A dermoscopy image of a single skin lesion: 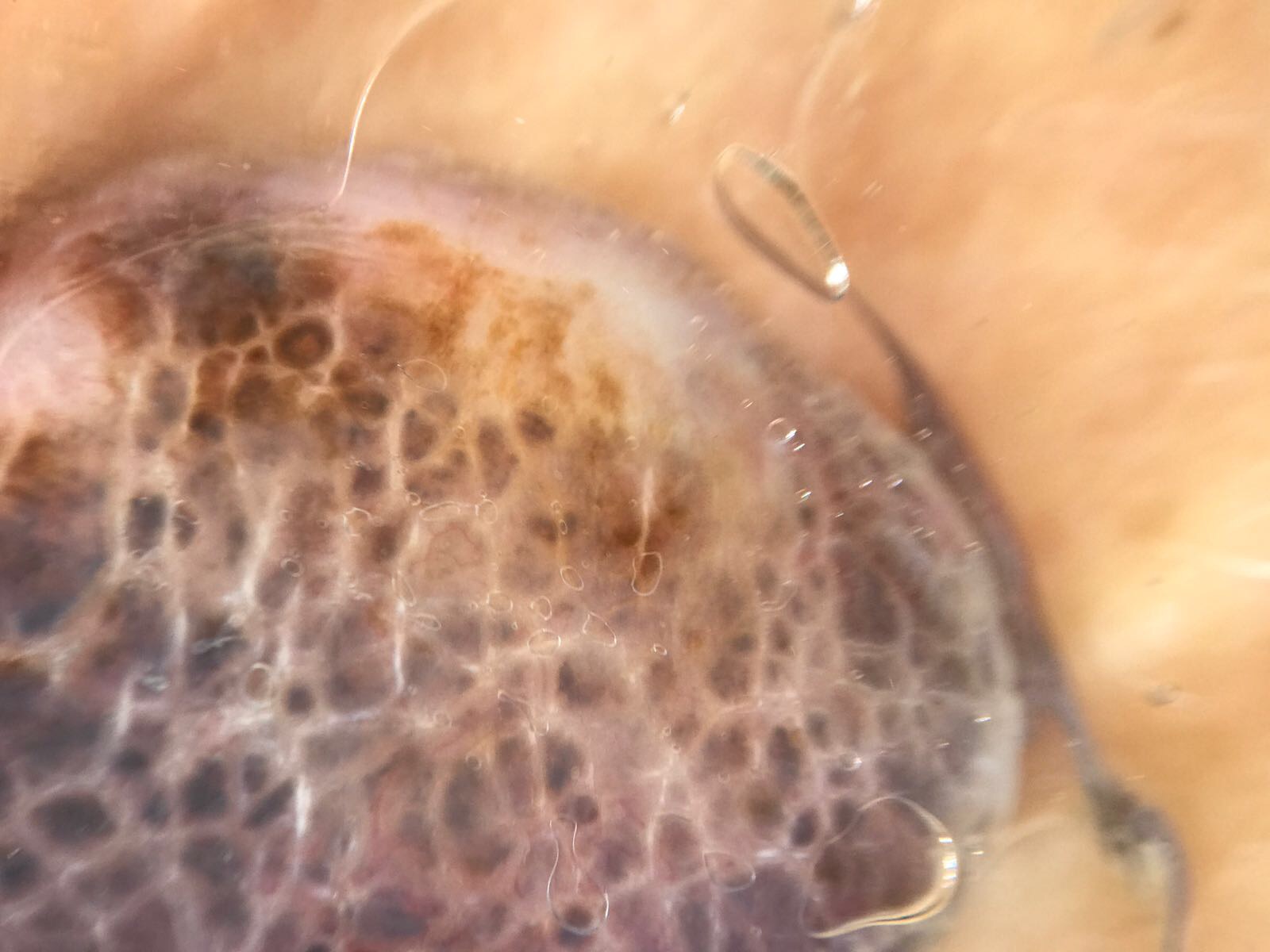Histopathology confirmed a melanoma.